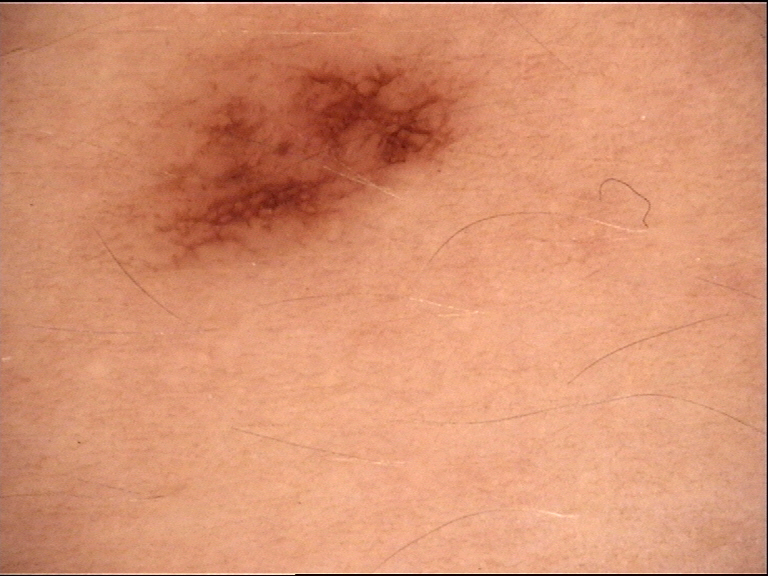Impression:
The diagnostic label was a dysplastic junctional nevus.